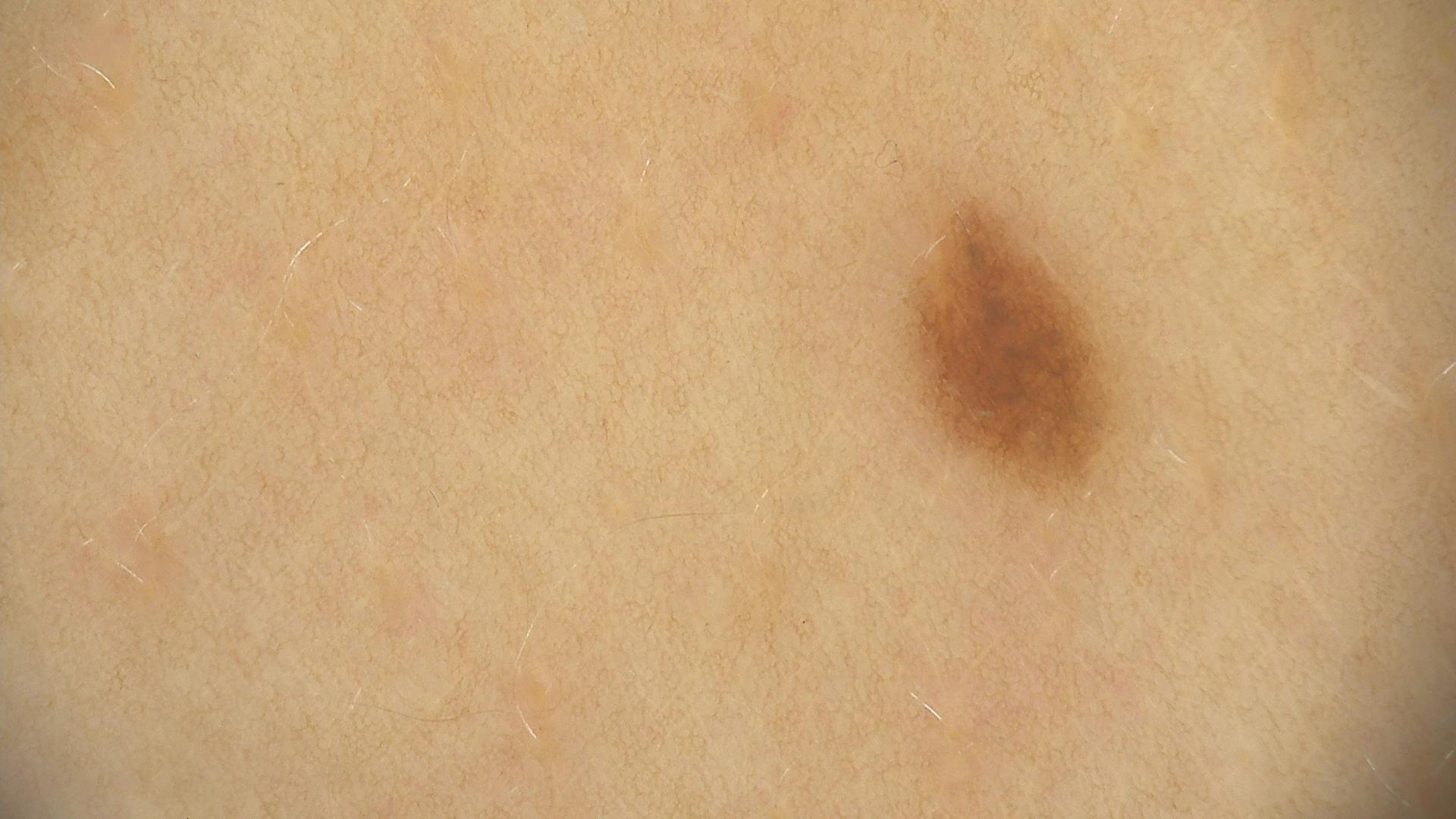A dermoscopic close-up of a skin lesion. Labeled as a dysplastic junctional nevus.